A clinical photograph of a skin lesion · a male subject age 56 · history notes tobacco use, pesticide exposure, prior malignancy (patient or family), no prior skin cancer (patient or family), and no alcohol use:
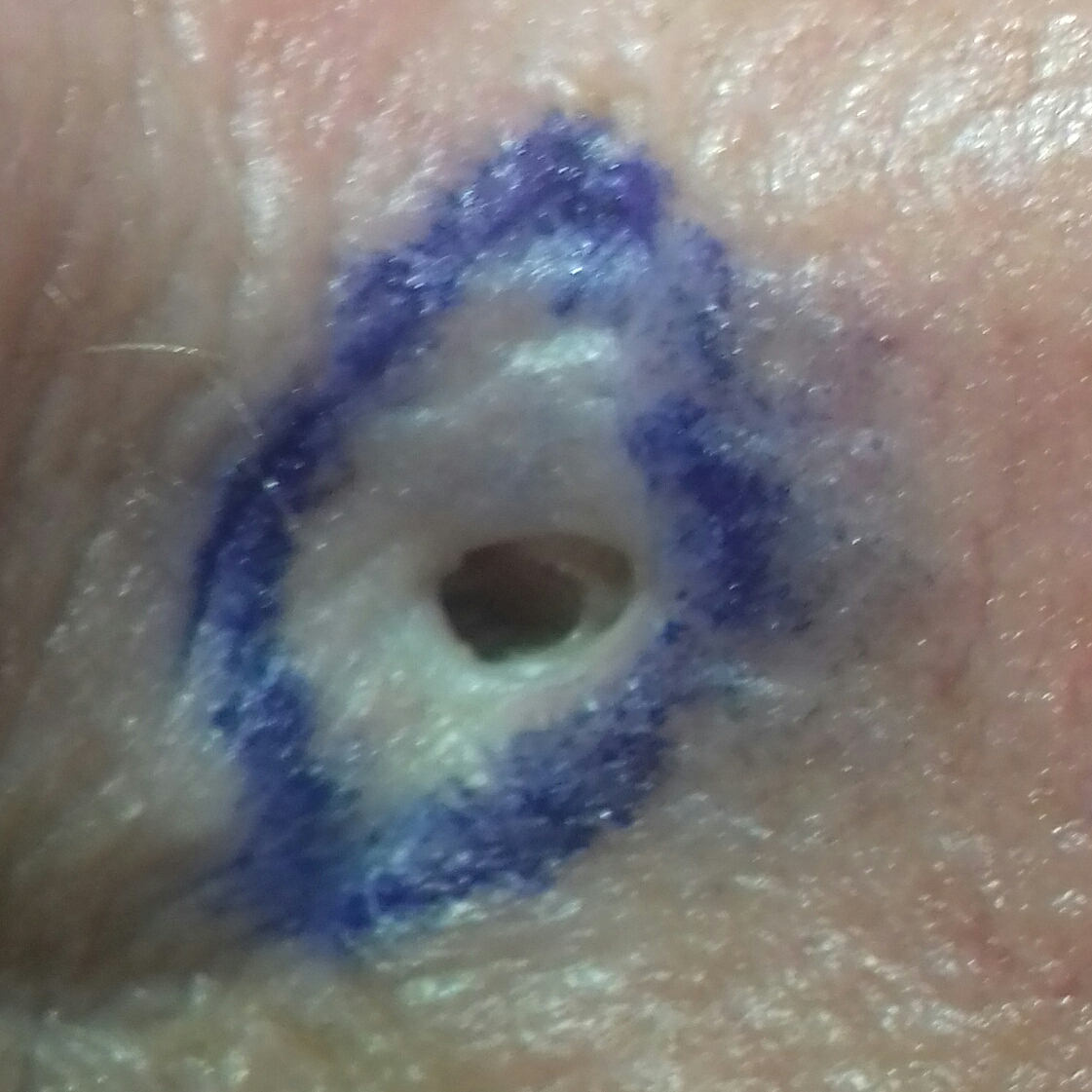Summary:
The lesion involves the nose. The lesion measures approximately 6 × 4 mm. Per patient report, the lesion hurts.
Conclusion:
Histopathologically confirmed as an actinic keratosis.